Dermoscopy of a skin lesion.
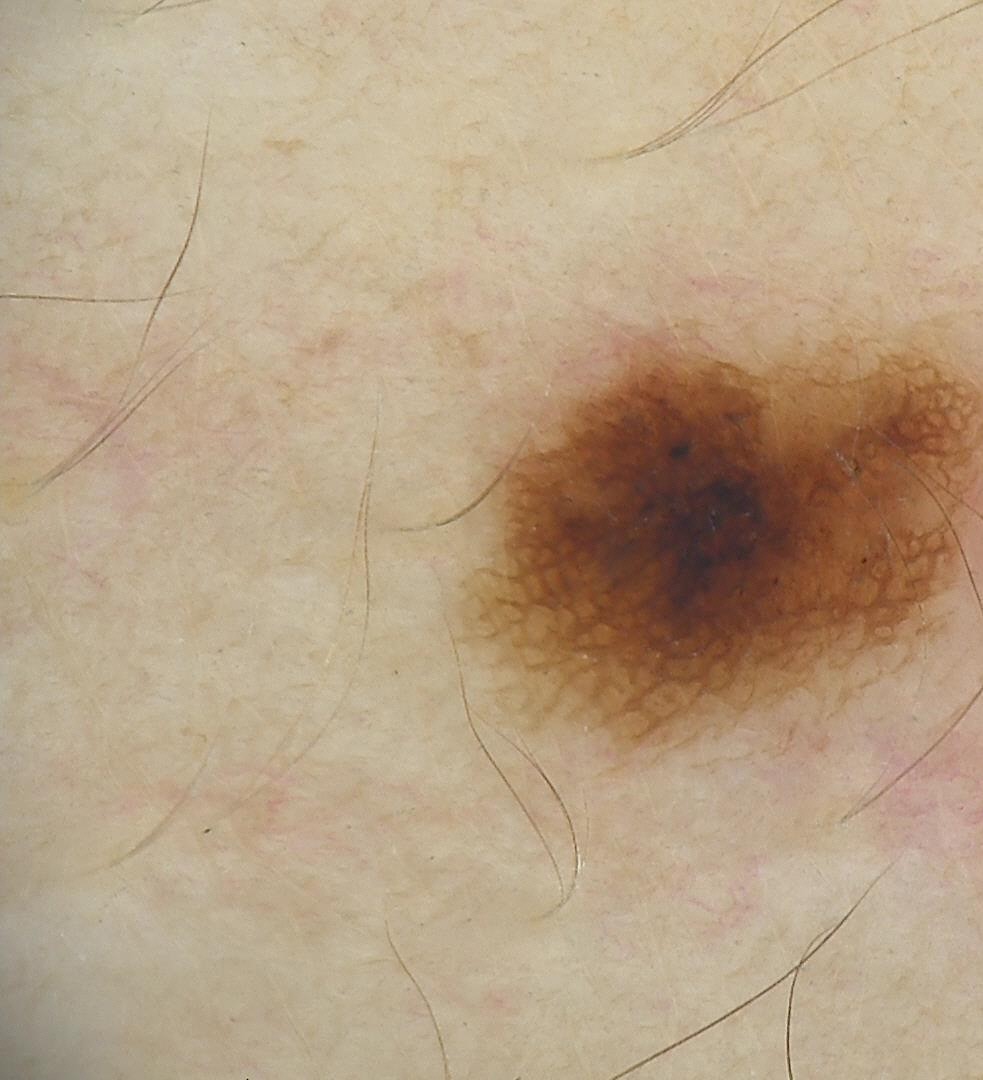– label — dysplastic junctional nevus (expert consensus)